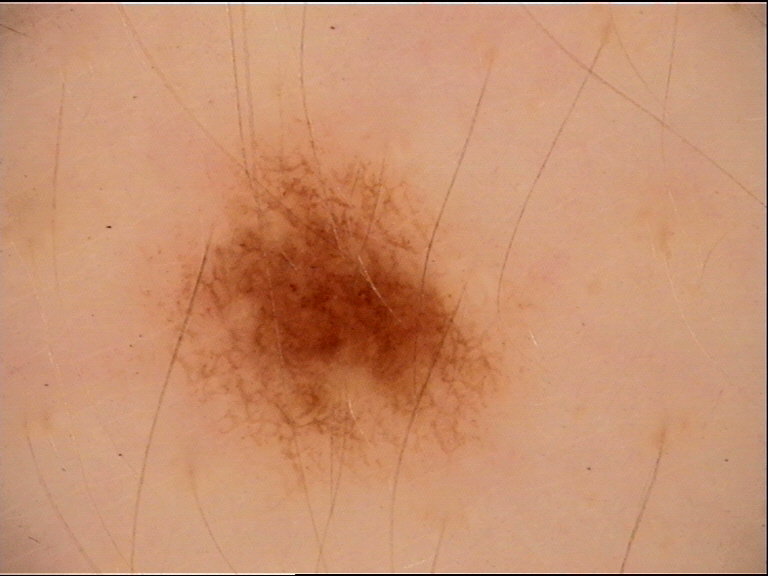Conclusion:
Diagnosed as a dysplastic junctional nevus.